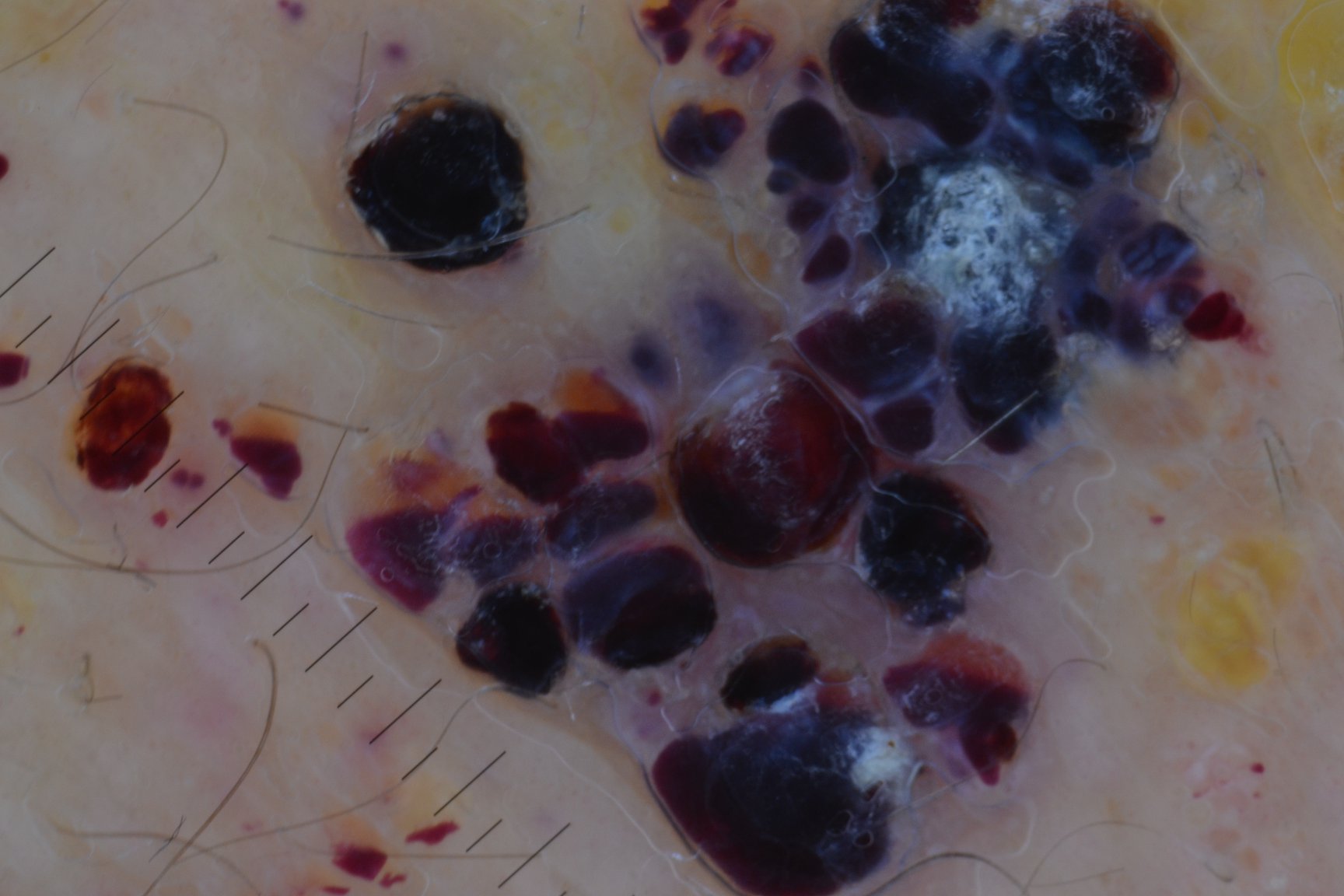Case: A dermatoscopic image of a skin lesion. Conclusion: Consistent with a vascular lesion — a lymphangioma.